The lesion is described as fluid-filled and raised or bumpy, the patient reports the condition has been present for about one day, the photo was captured at an angle, the contributor is female, the affected area is the leg, the patient described the issue as a rash, Fitzpatrick I, symptoms reported: burning and itching — 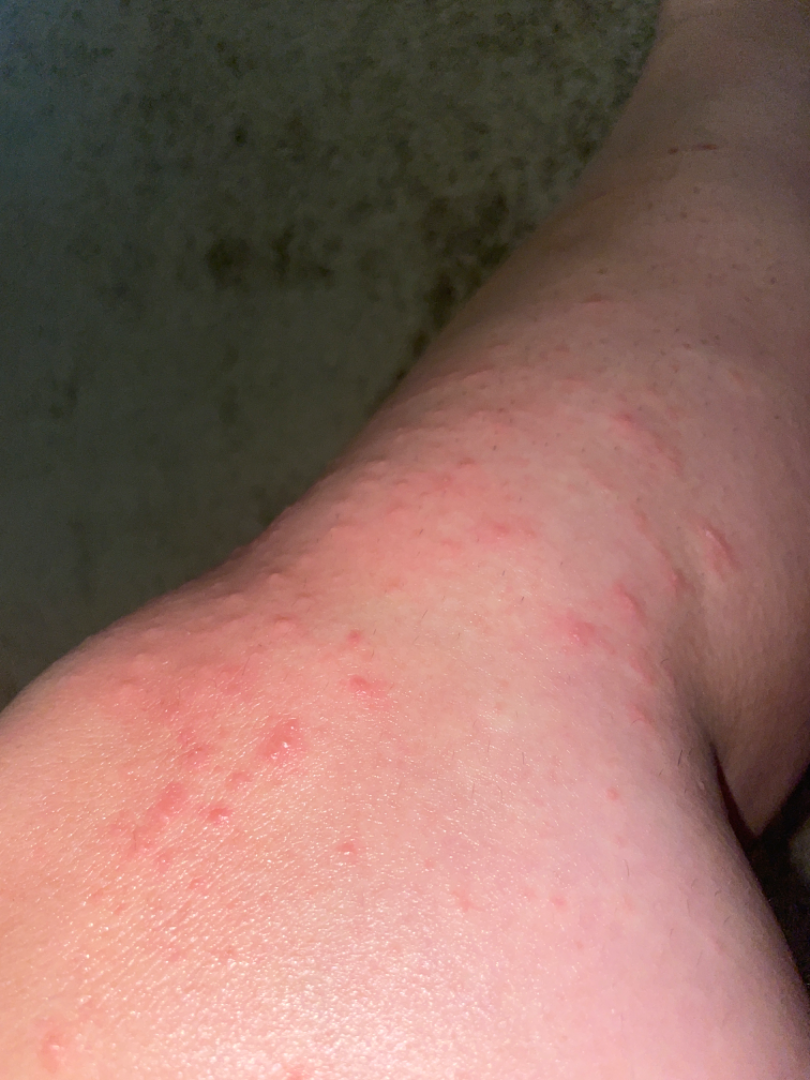Review:
Most likely Eczema; also on the differential is Insect Bite; also consider Allergic Contact Dermatitis.